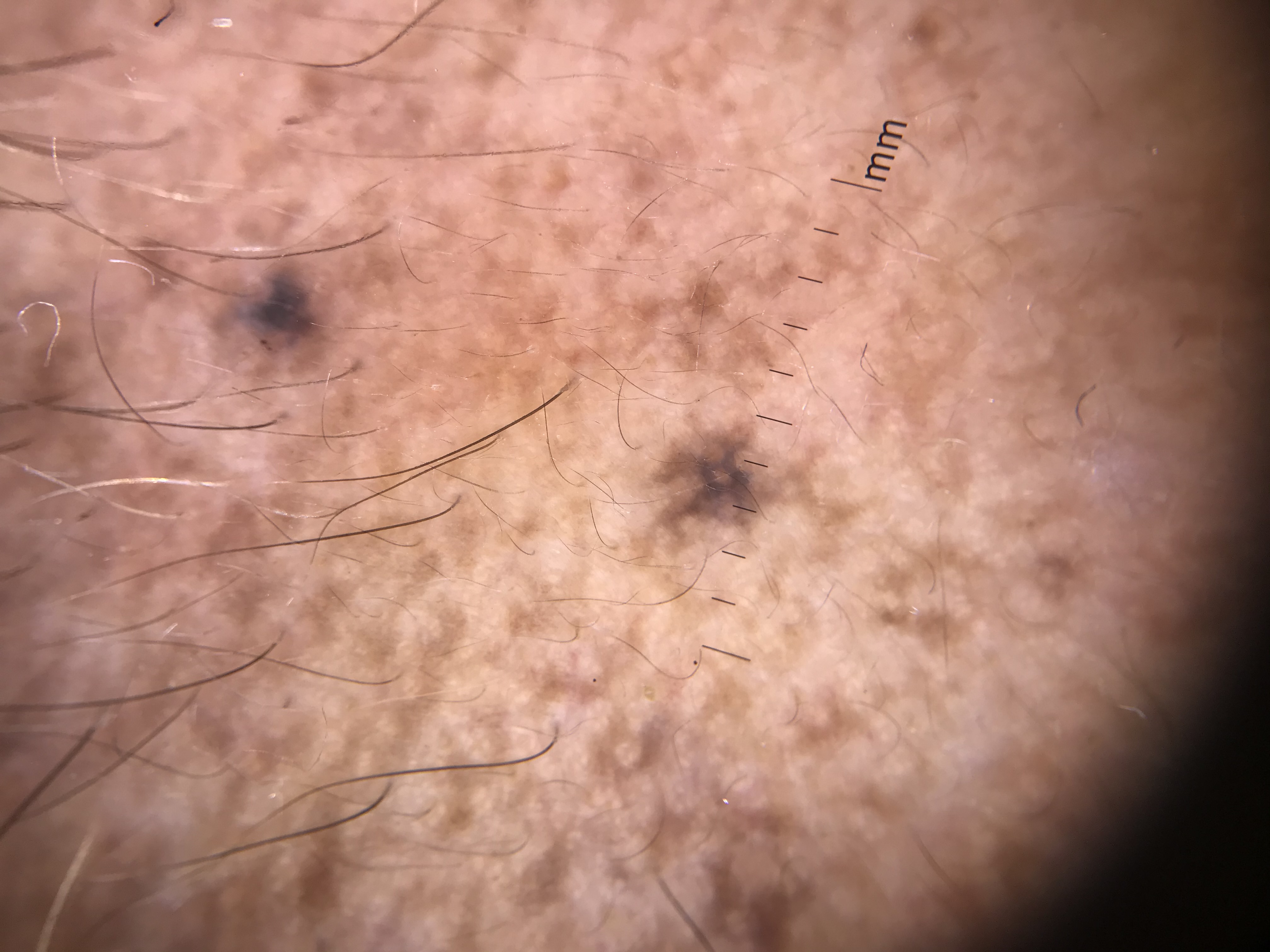imaging: dermoscopy | classification: dermal, banal | class: blue nevus (expert consensus).